The photo was captured at an angle — 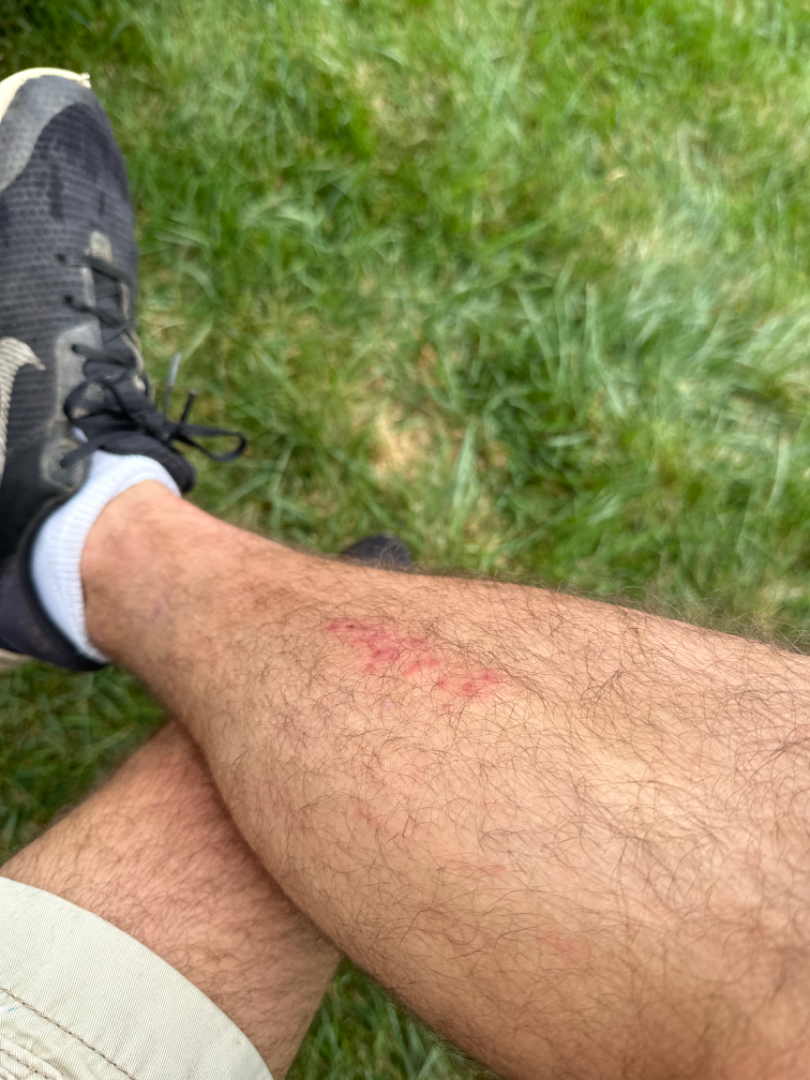* impression — single-reviewer assessment: the differential includes Folliculitis, Eczema and Allergic Contact Dermatitis, with no clear leading consideration